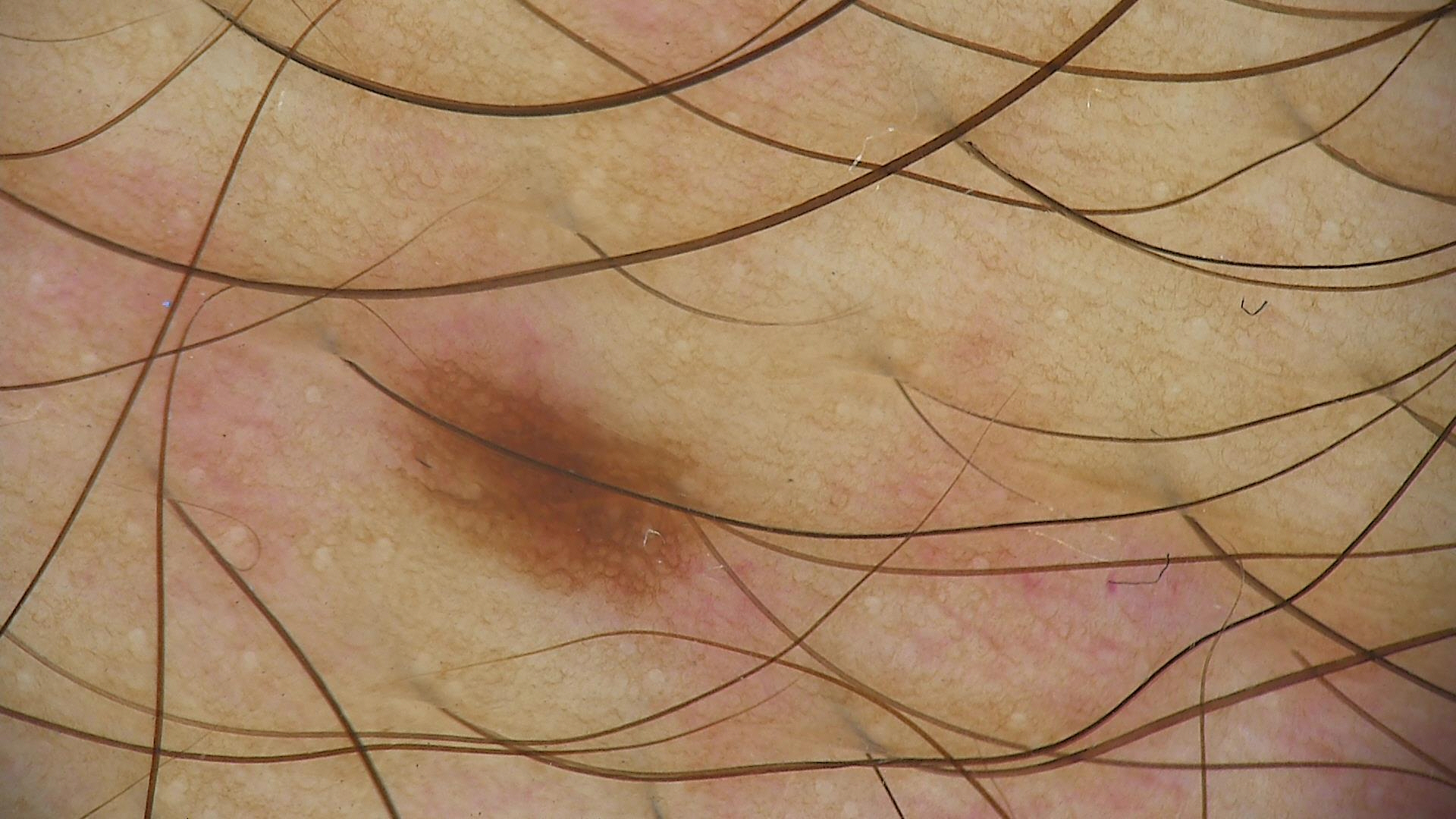Findings:
The architecture is that of a banal lesion.
Impression:
The diagnostic label was a junctional nevus.